A skin lesion imaged with a dermatoscope.
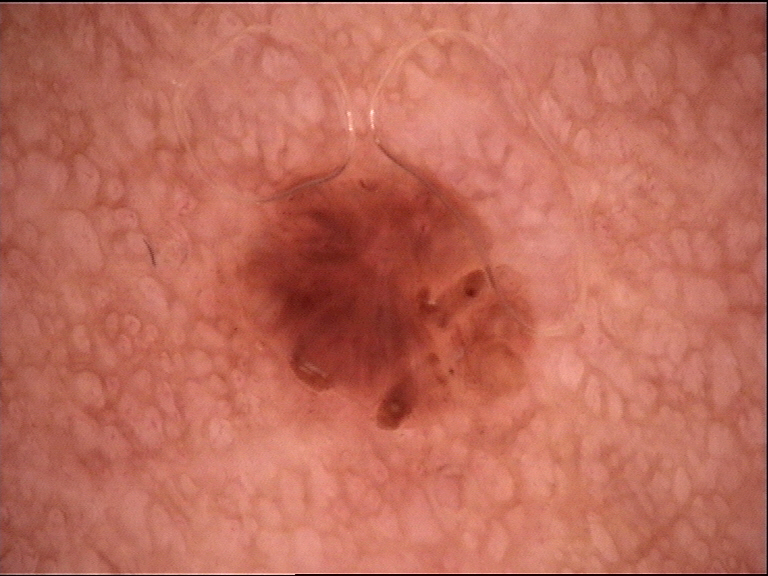Summary:
This is a banal lesion.
Conclusion:
Labeled as a compound nevus.